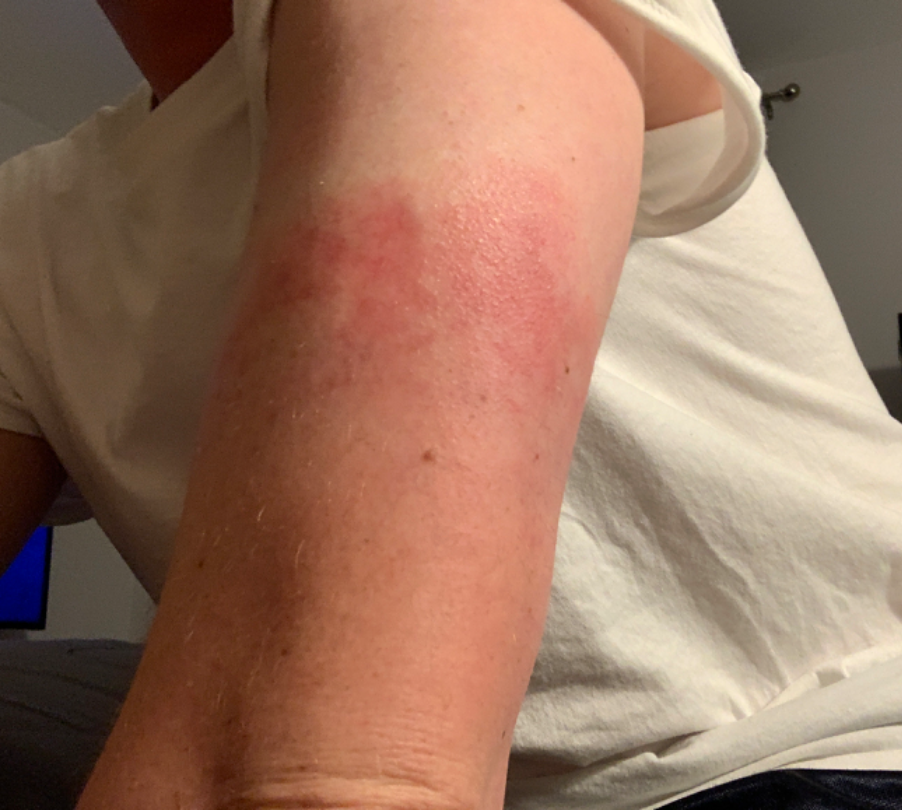The dermatologist could not determine a likely condition from the photograph alone. An image taken at a distance. The patient notes the condition has been present for one to four weeks. Texture is reported as flat. The lesion involves the arm.